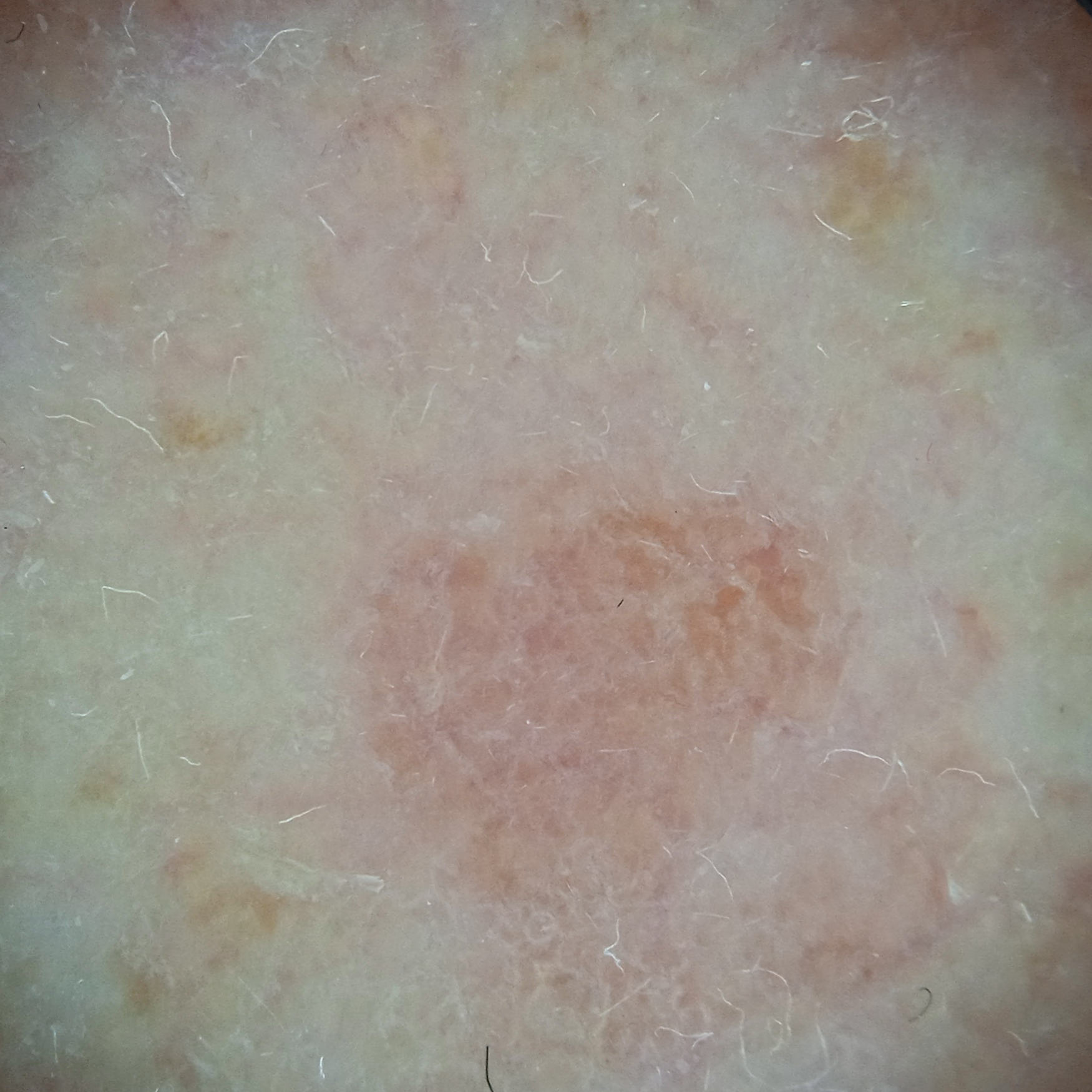The patient reports immunosuppression, a prior organ transplant, and no personal history of skin cancer.
A moderate number of moles by the patient's own estimate.
A female patient aged 55.
The patient says their skin reddens painfully with sun exposure.
The referring clinician suspected basal cell carcinoma.
The lesion involves the face.
Measuring roughly 5.7 mm.
The consensus diagnosis for this lesion was an actinic keratosis.